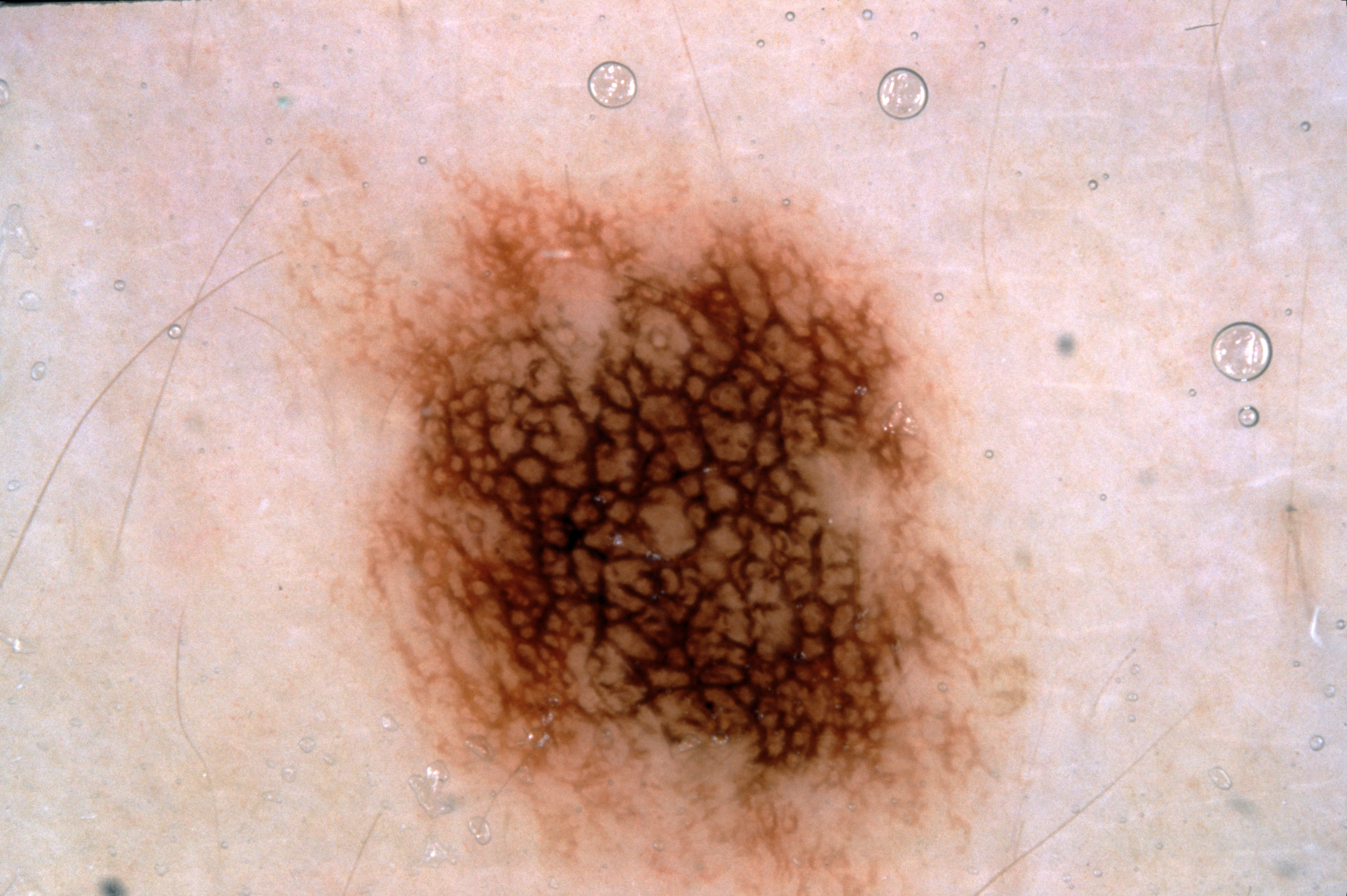A female patient aged approximately 15.
A dermoscopy image of a single skin lesion.
The lesion takes up about 35% of the image.
On dermoscopy, the lesion shows pigment network; no milia-like cysts, negative network, or streaks.
The lesion runs off the edge of the field of view.
The lesion occupies the region x1=230, y1=129, x2=1040, y2=895.
Expert review diagnosed this as a melanocytic nevus, a benign lesion.